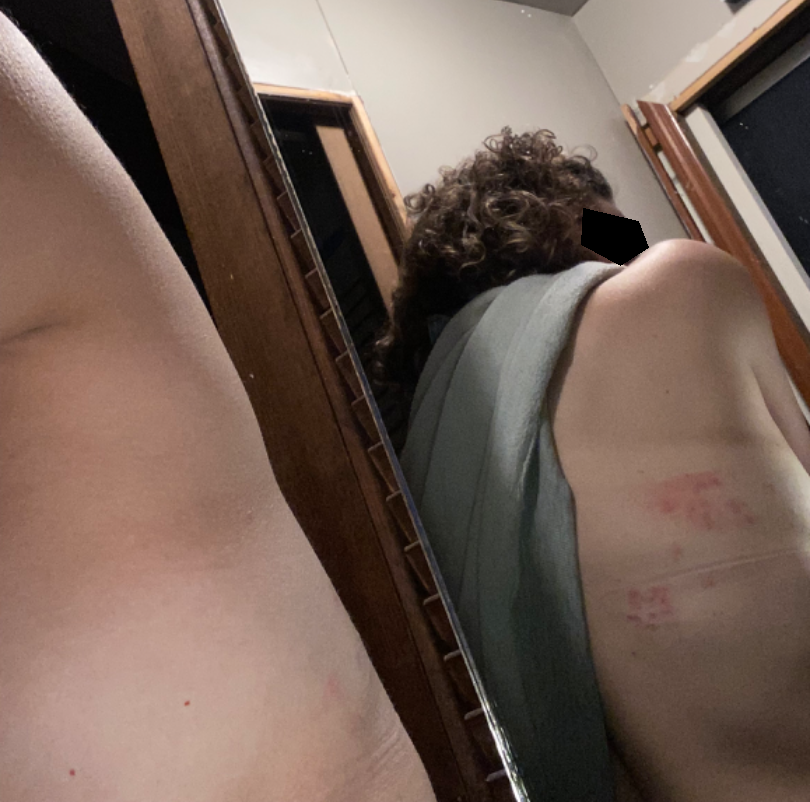reported symptoms=itching
patient=female, age 50–59
photo taken=at an angle
surface texture=raised or bumpy
other reported symptoms=none reported
affected area=back of the torso
duration=less than one week
clinical impression=reviewed remotely by one dermatologist: most consistent with Herpes Zoster; with consideration of Allergic Contact Dermatitis; also raised was Herpes Simplex